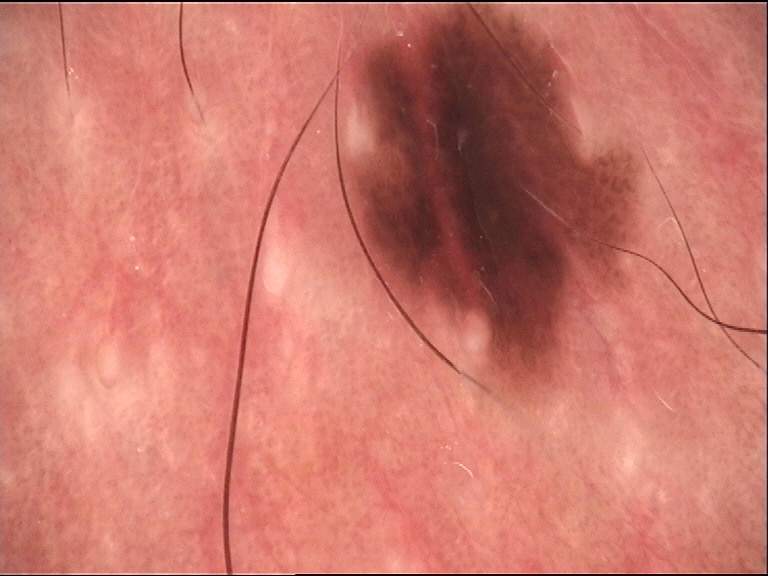Q: What is this lesion?
A: dysplastic junctional nevus (expert consensus)